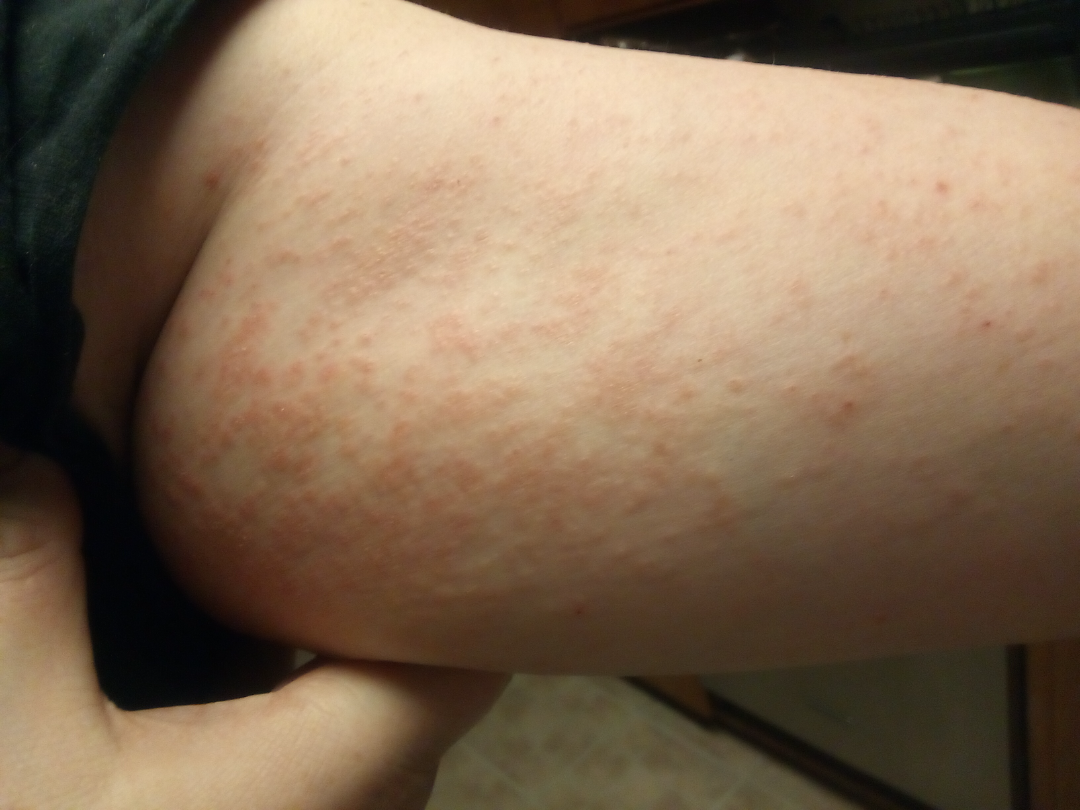The skin condition could not be confidently assessed from this image.